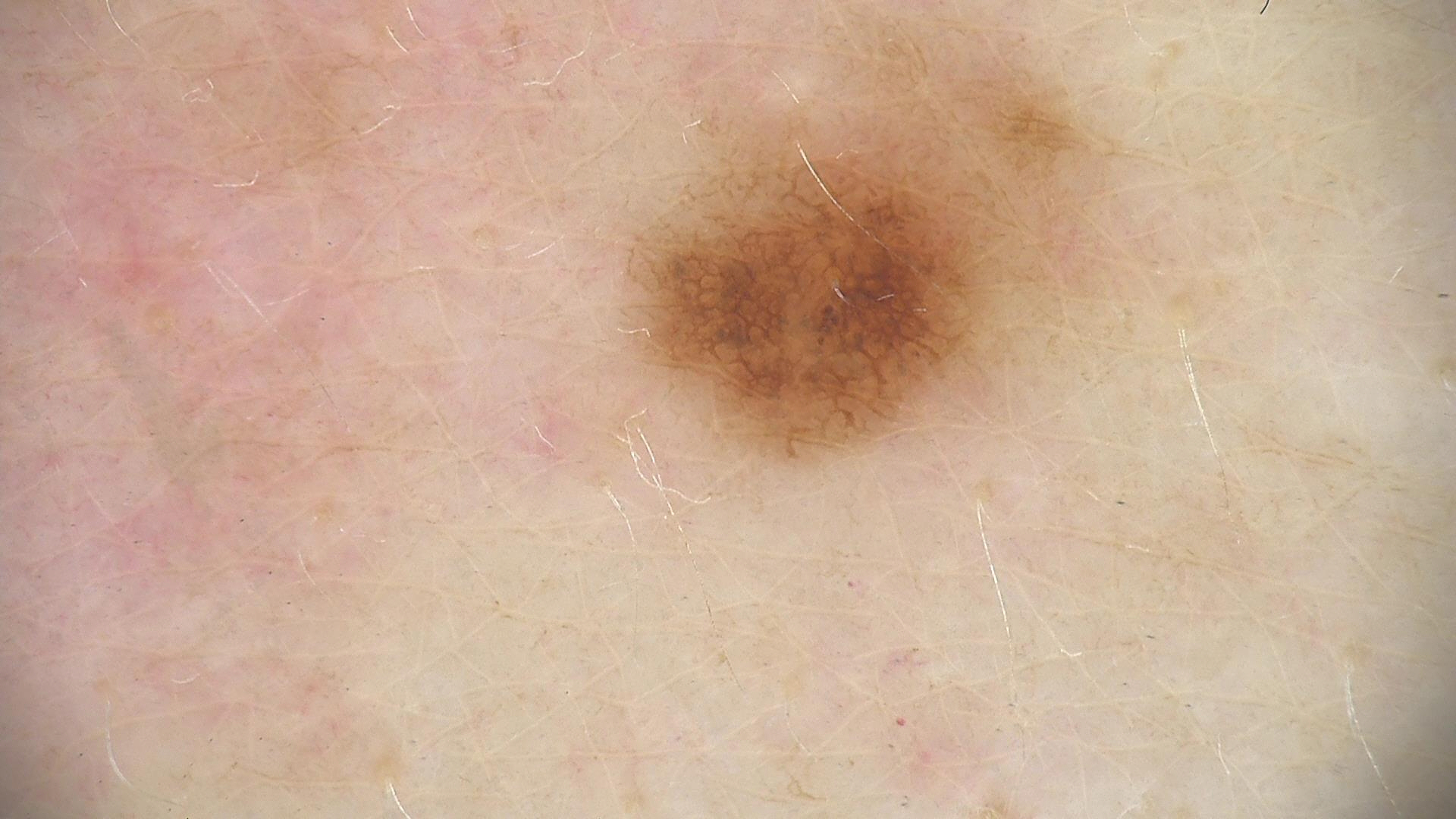diagnosis:
  name: dysplastic junctional nevus
  code: jd
  malignancy: benign
  super_class: melanocytic
  confirmation: expert consensus